A skin lesion imaged with a dermatoscope. The patient says their skin tans without first burning. Imaged for a research study, with no referral diagnosis recorded. A female subject age 92. On a questionnaire the patient reported a family history of skin cancer and a personal history of cancer: 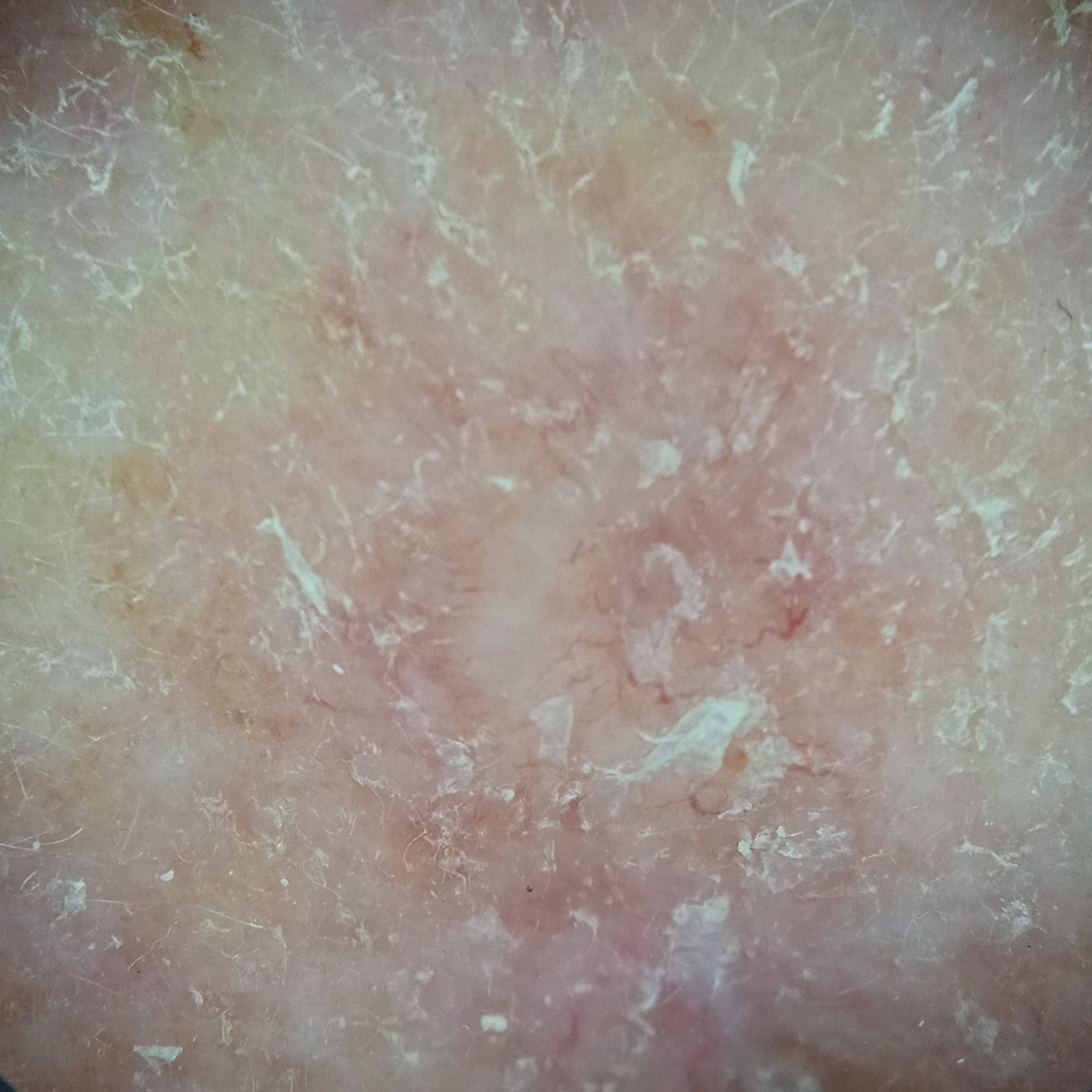Summary:
Located on the face. Measuring roughly 7 mm.
Conclusion:
The dermatologists' assessment was a basal cell carcinoma.